A dermoscopic image of a skin lesion.
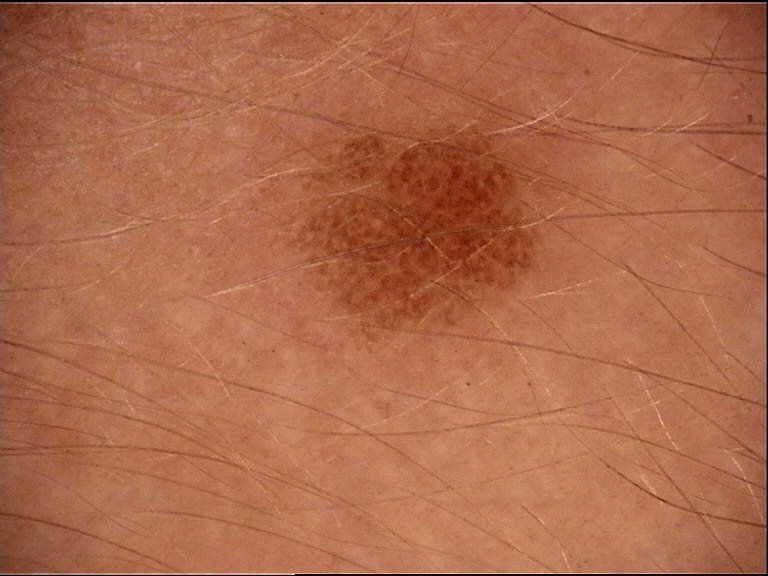Diagnosed as a banal lesion — a junctional nevus.